The arm, front of the torso and leg are involved · the photograph is a close-up of the affected area · male contributor, age 18–29 — 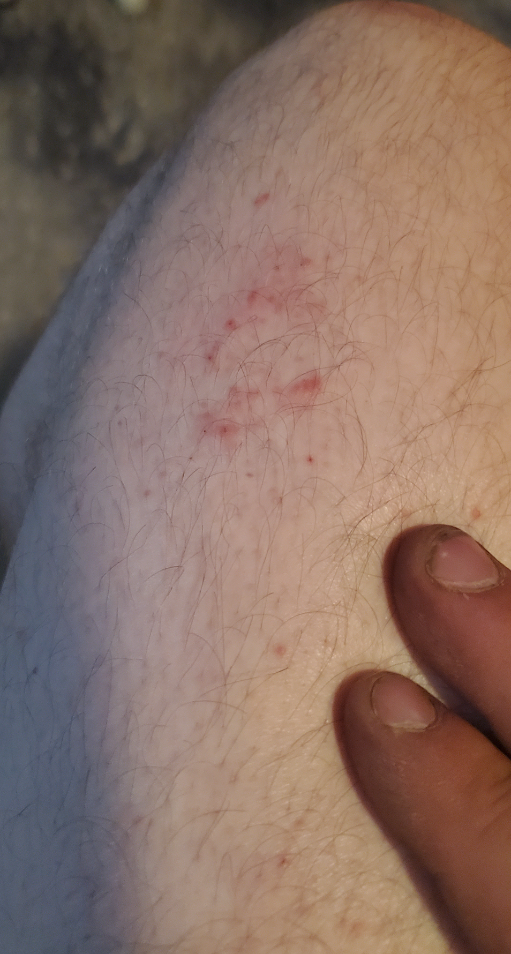{"assessment": "could not be assessed", "symptoms": ["enlargement", "itching"], "duration": "one to four weeks", "texture": "raised or bumpy", "patient_category": "a rash", "systemic_symptoms": "none reported"}